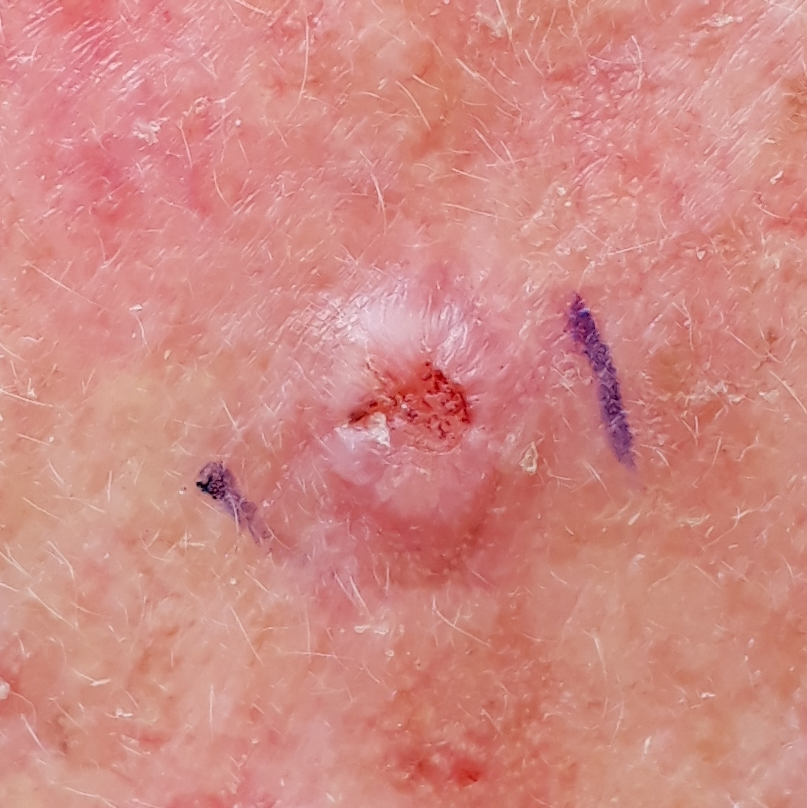Summary:
History notes prior malignancy (patient or family) and prior skin cancer (patient or family). A female patient in their mid-60s. Recorded as skin type II. A clinical photo of a skin lesion taken with a smartphone. The lesion is on the face. The patient describes that the lesion itches, has grown, is elevated, has bled, and hurts, but has not changed.
Pathology:
The biopsy diagnosis was a malignant lesion — a squamous cell carcinoma.